The photograph was taken at a distance:
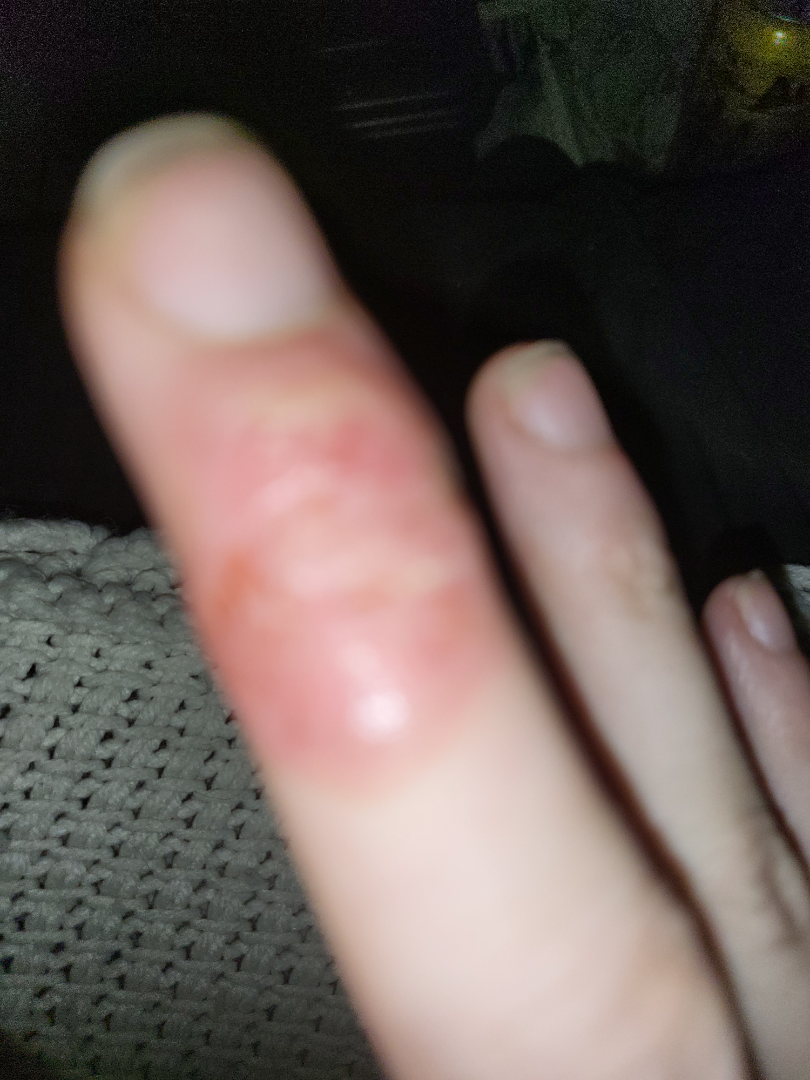On remote review of the image, most likely Herpes Simplex; an alternative is Skin and soft tissue atypical mycobacterial infection; less likely is Allergic Contact Dermatitis.